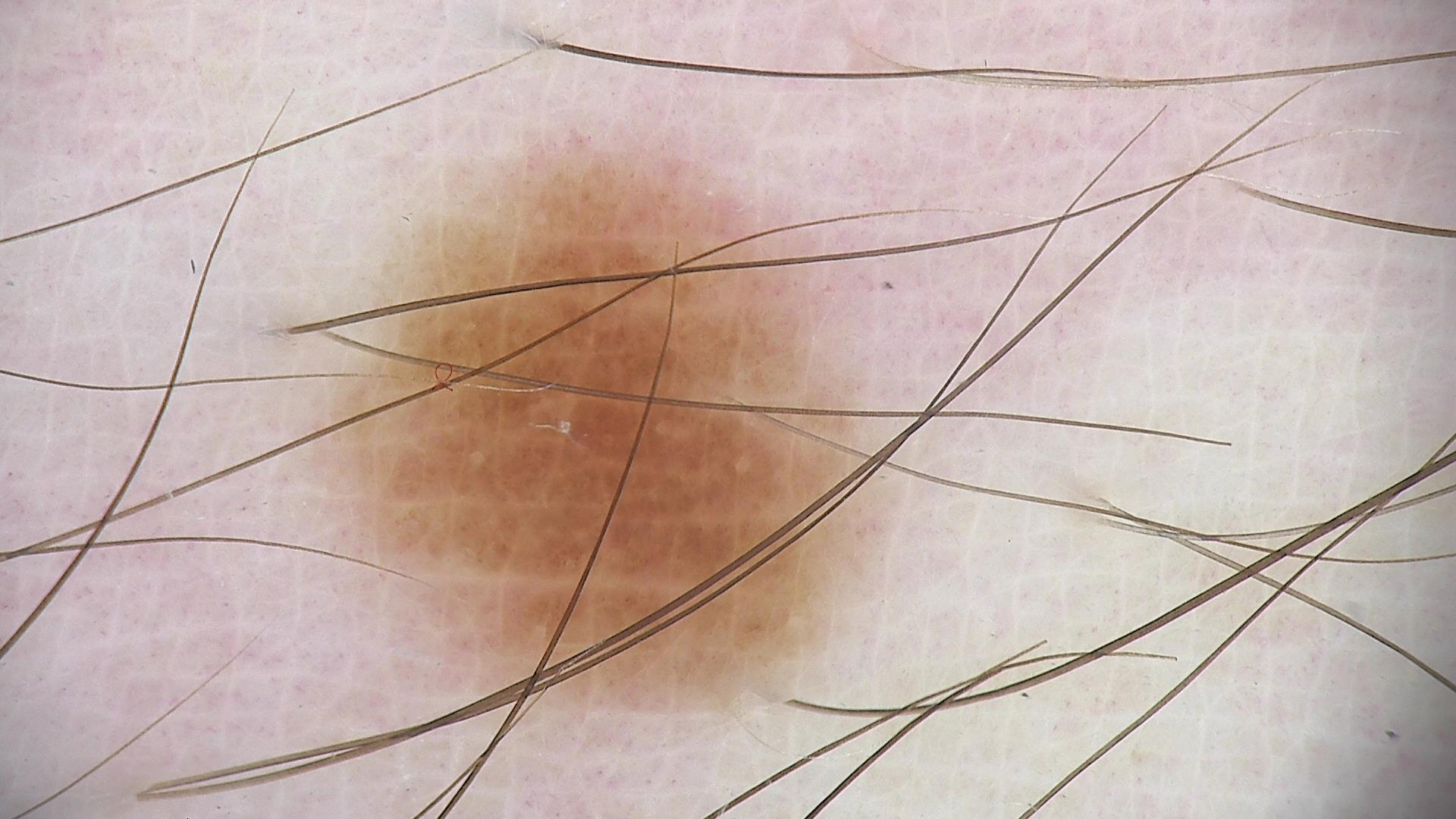Consistent with a dysplastic junctional nevus.